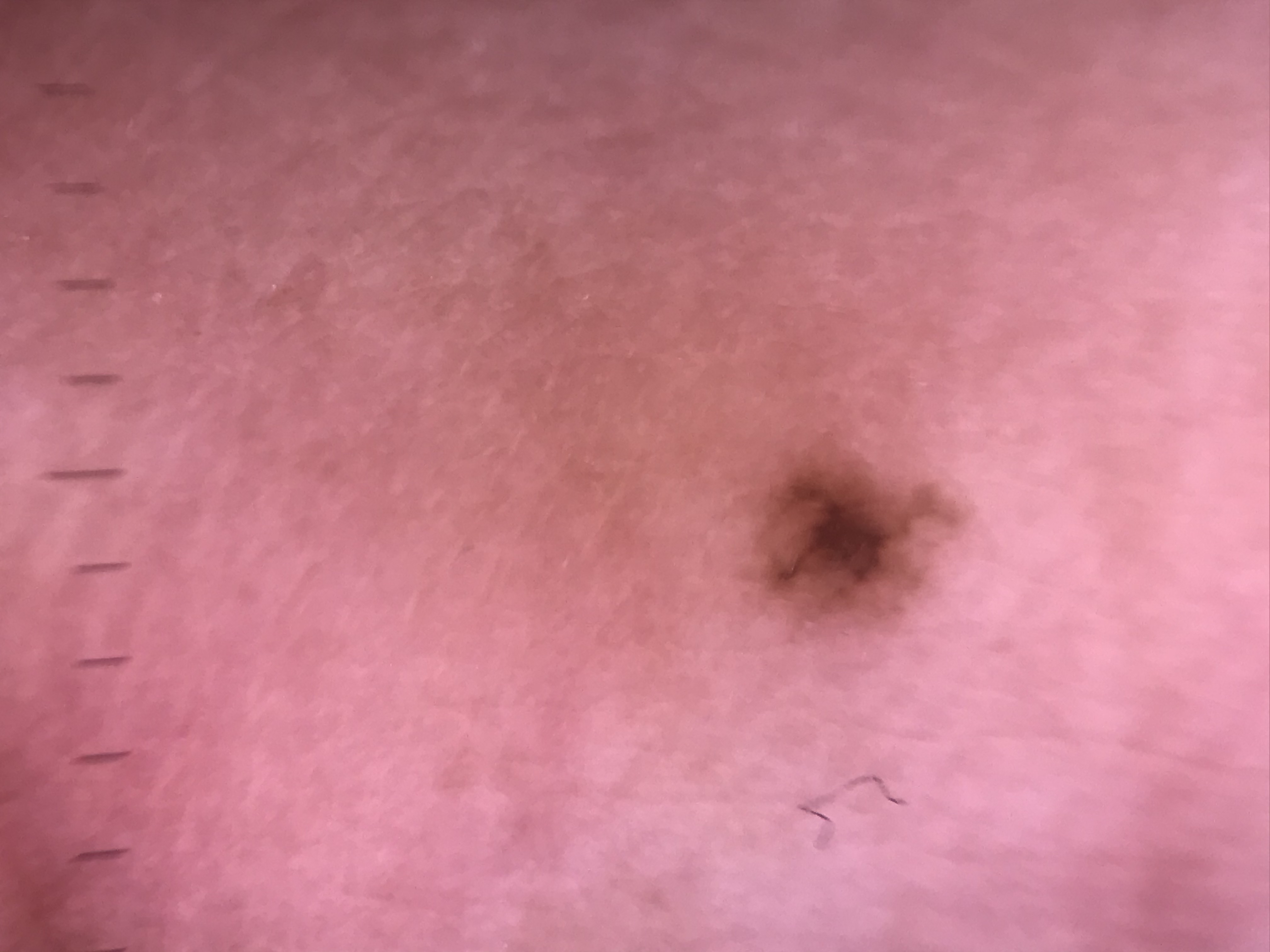imaging = dermoscopy, diagnostic label = acral junctional nevus (expert consensus).